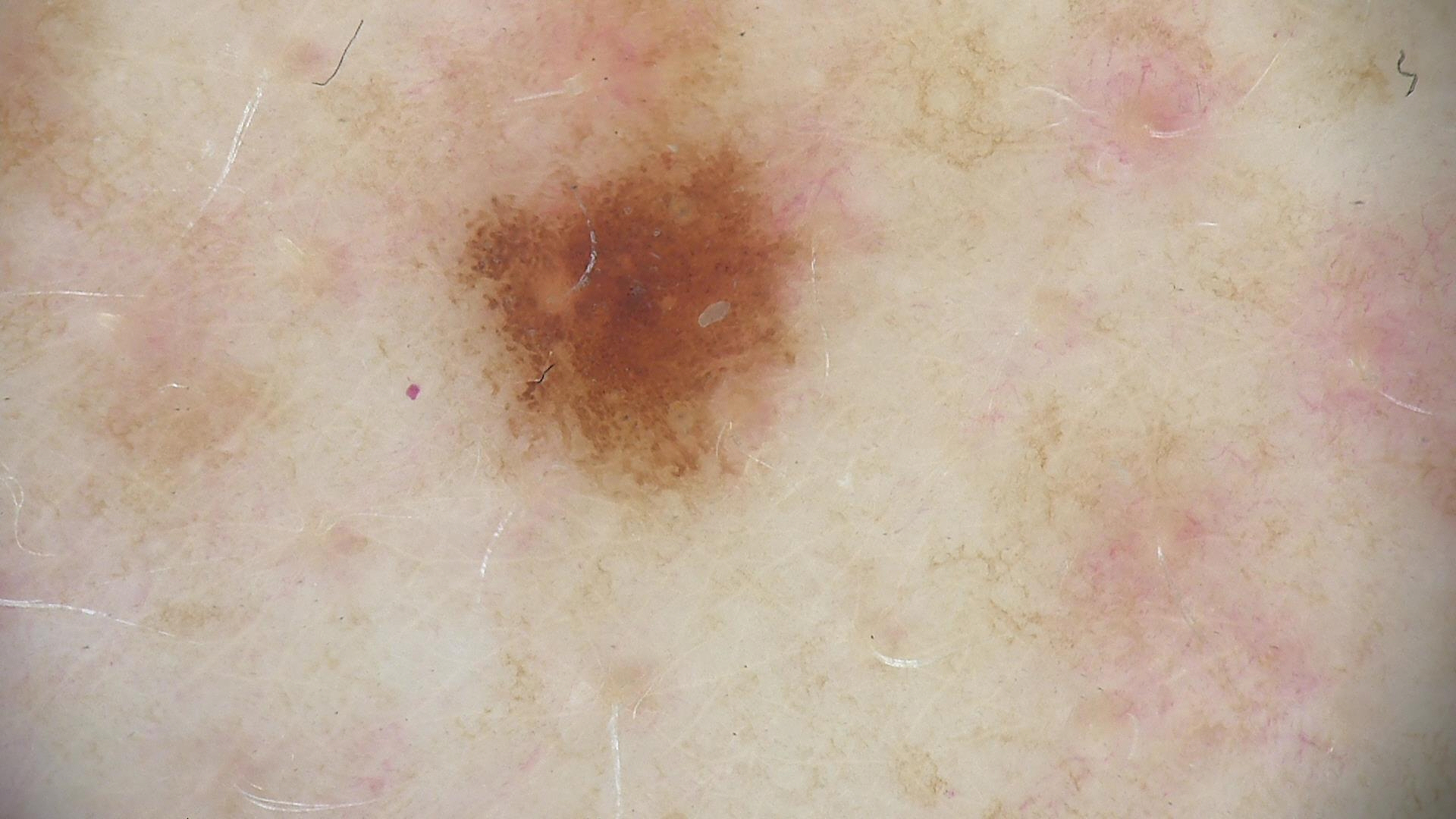Conclusion: Consistent with a dysplastic junctional nevus.